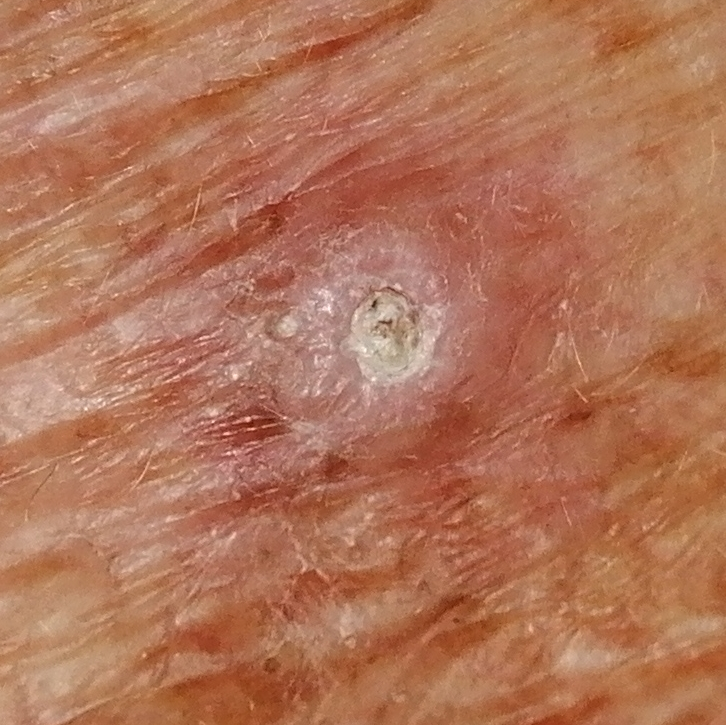A clinical photograph of a skin lesion. Histopathologically confirmed as a squamous cell carcinoma.